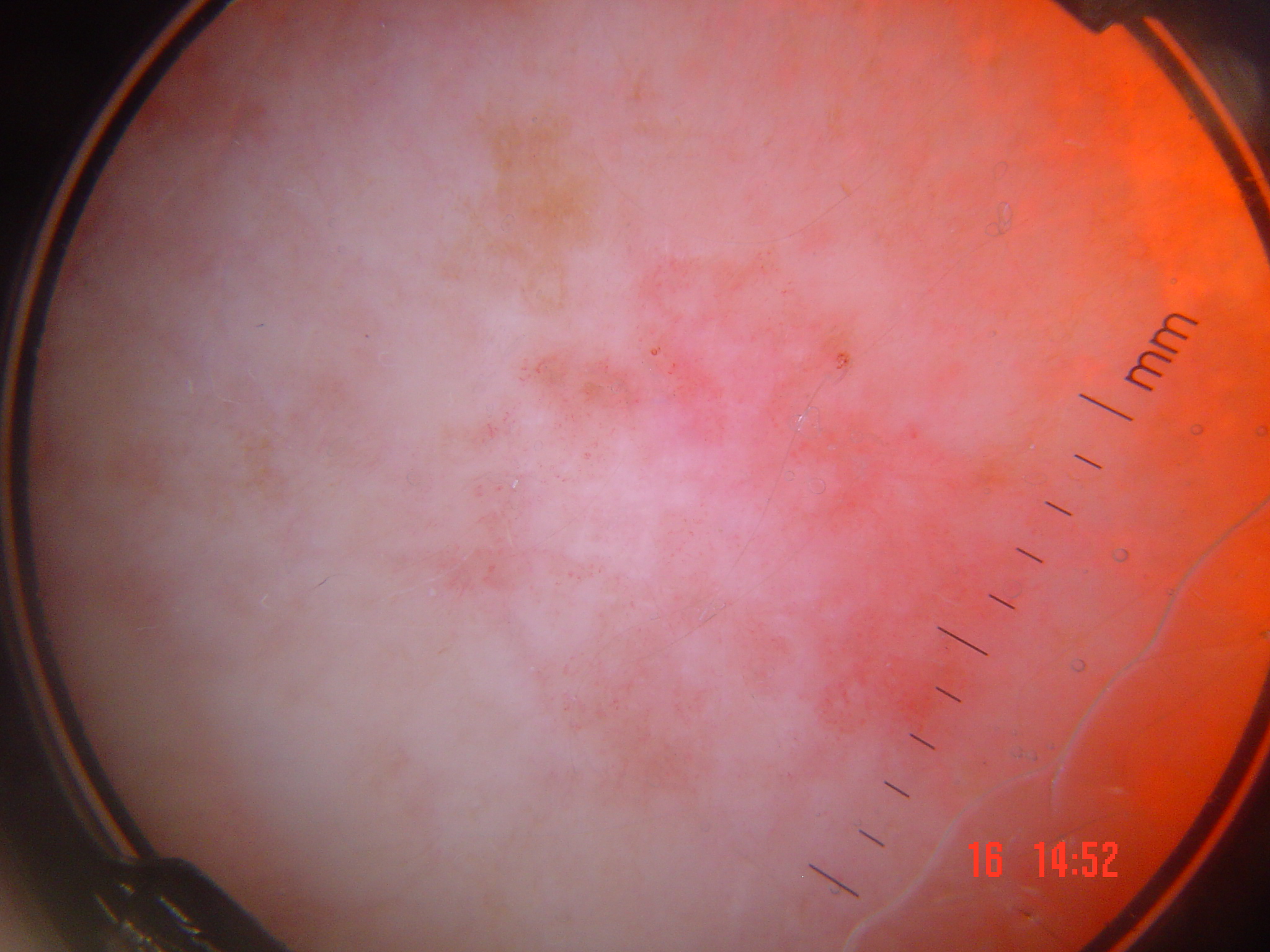class — Bowen's disease (biopsy-proven)